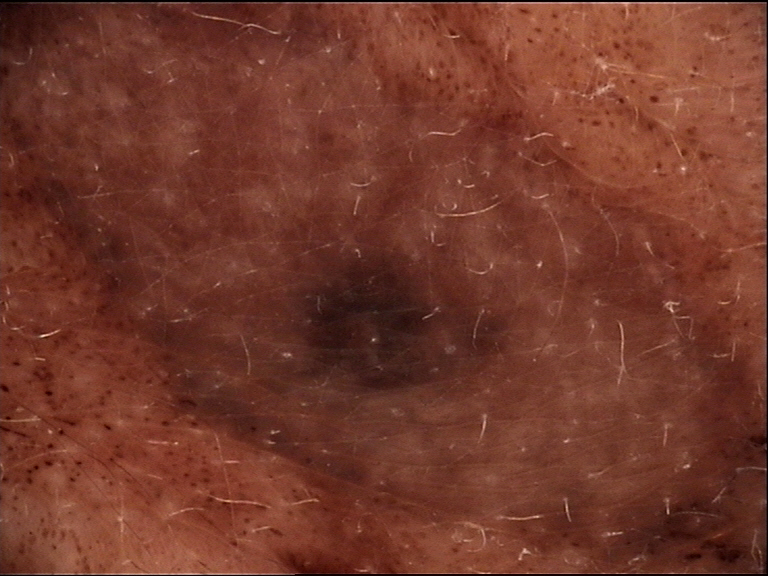subtype = banal | assessment = congenital compound nevus (expert consensus).